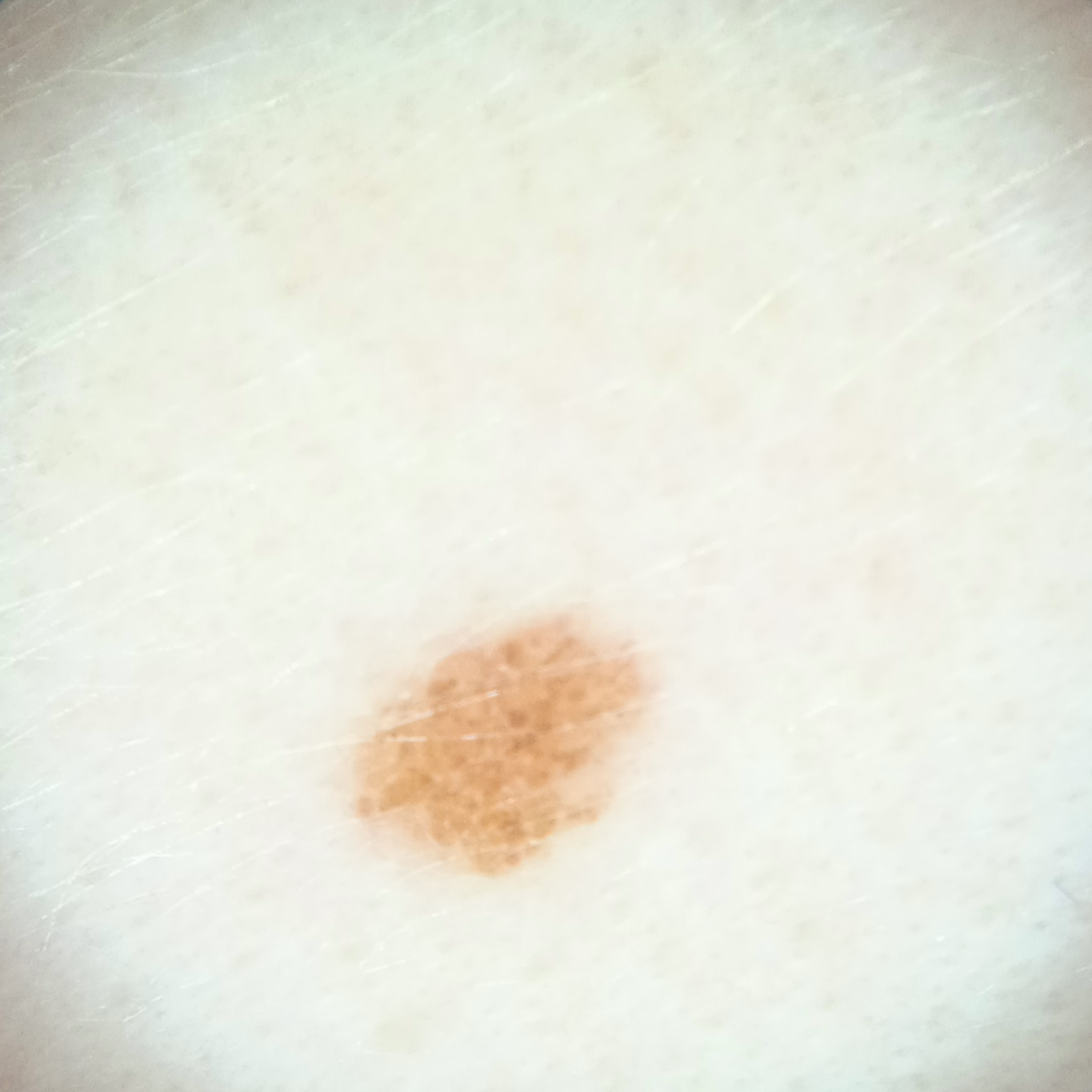Few moles overall by the patient's own estimate. A dermoscopy image of a skin lesion. The patient says their skin reddens with sun exposure. A female patient 15 years old. On a questionnaire the patient reported no prior organ transplant and no sunbed use. The lesion is located on the face. Dermatologist review favored a melanocytic nevus.